A dermatoscopic image of a skin lesion. The patient is skin type II. A female patient aged approximately 50 — 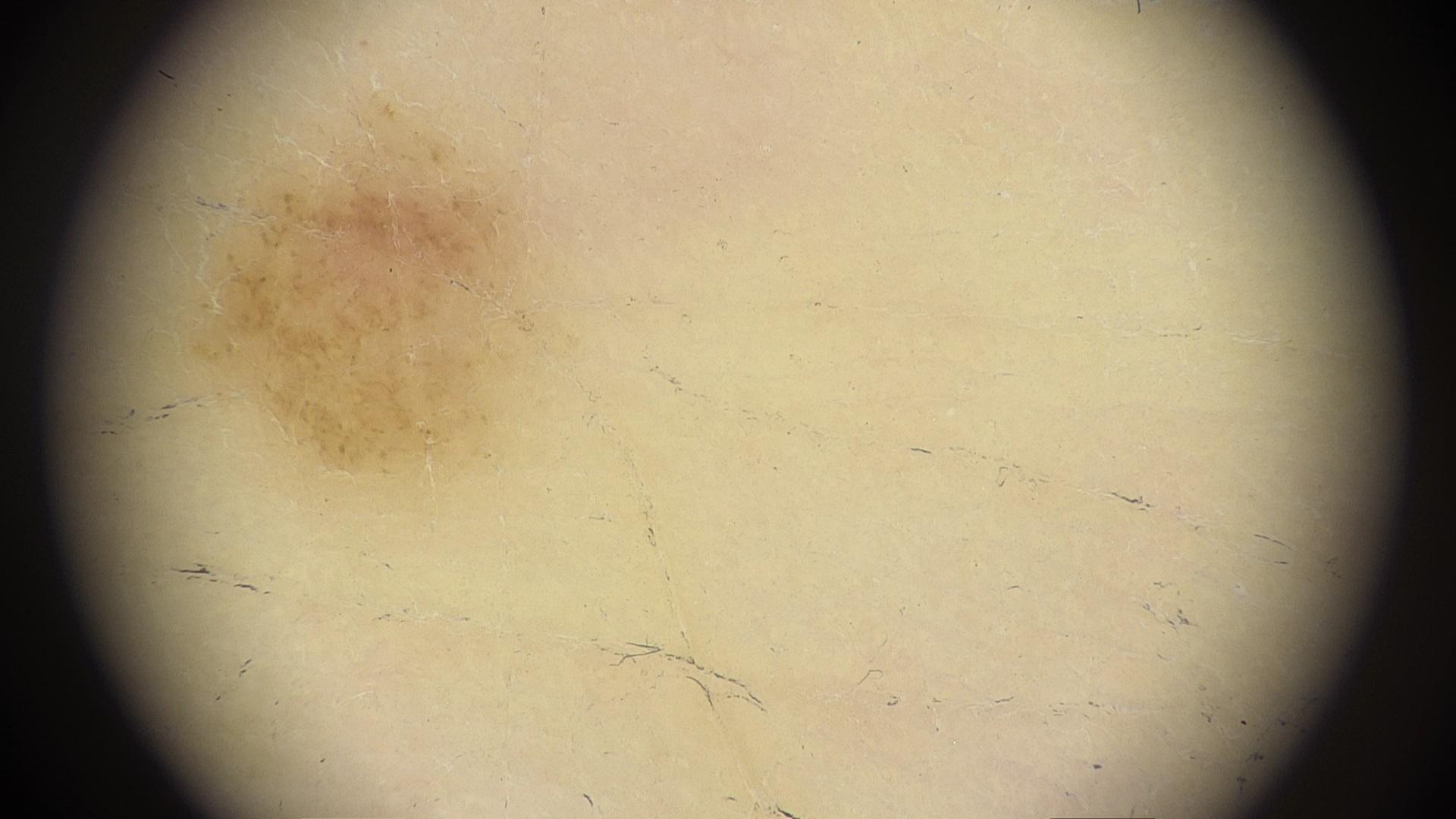Case summary:
The lesion is located on a lower extremity.
Conclusion:
The diagnostic impression was a nevus.